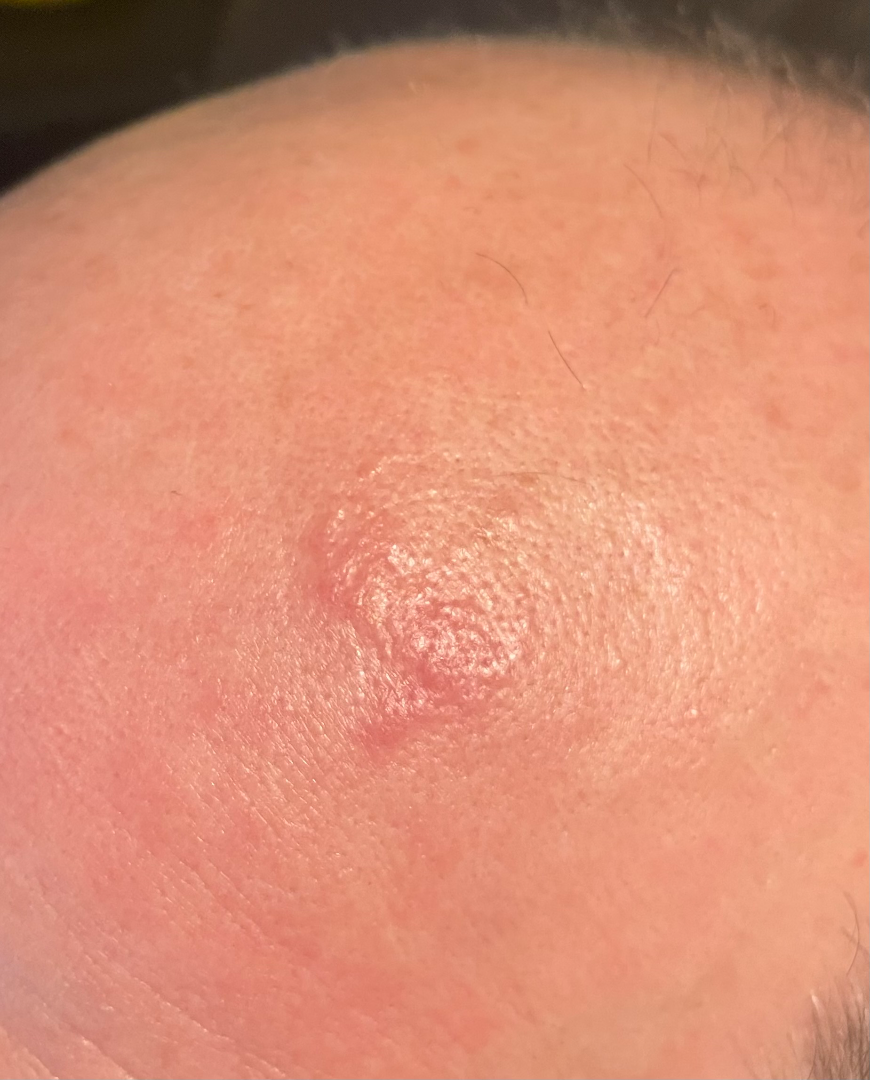assessment: unable to determine
location: head or neck
skin tone: human graders estimated a Monk skin tone scale of 2
image framing: at an angle
lesion texture: fluid-filled and raised or bumpy